The contributor is a male aged 30–39 · located on the back of the torso, front of the torso and arm · the photo was captured at an angle — 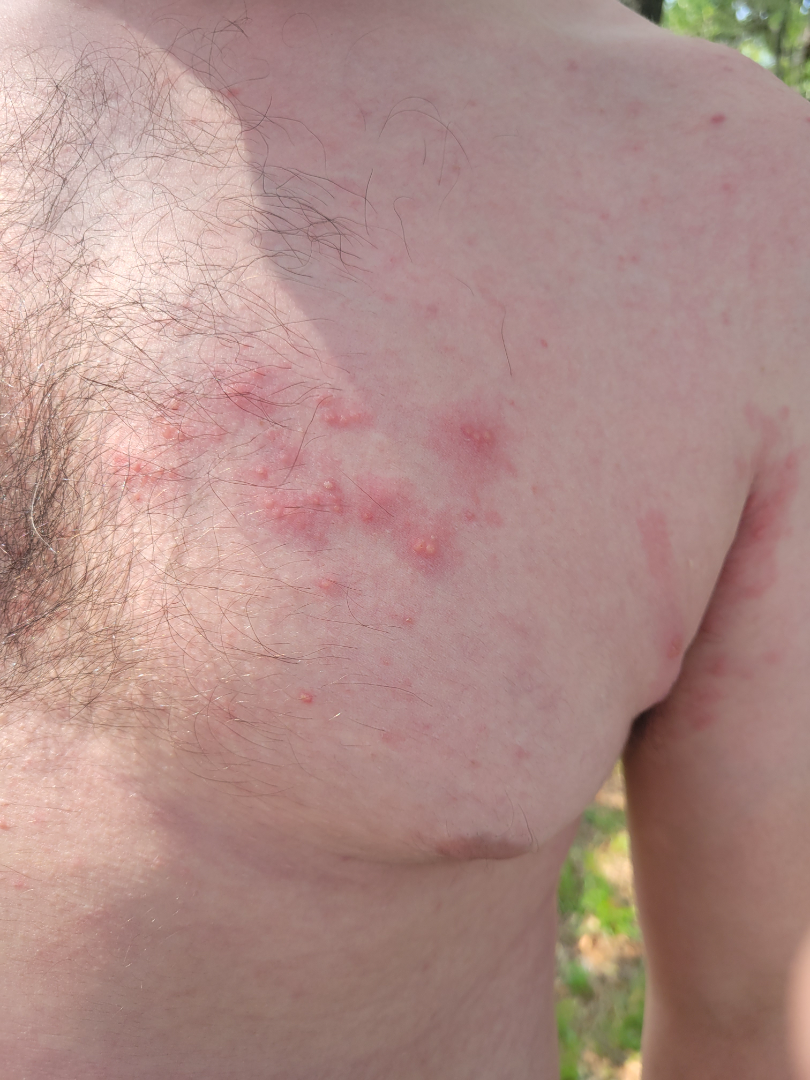Background:
Present for less than one week. The lesion is described as fluid-filled. The patient described the issue as a rash. The lesion is associated with burning, bothersome appearance, itching and pain. Skin tone: FST II; lay reviewers estimated 2 on the Monk skin tone scale.
Findings:
On dermatologist assessment of the image, the differential includes Herpes Zoster and Herpes Simplex, with no clear leading consideration.